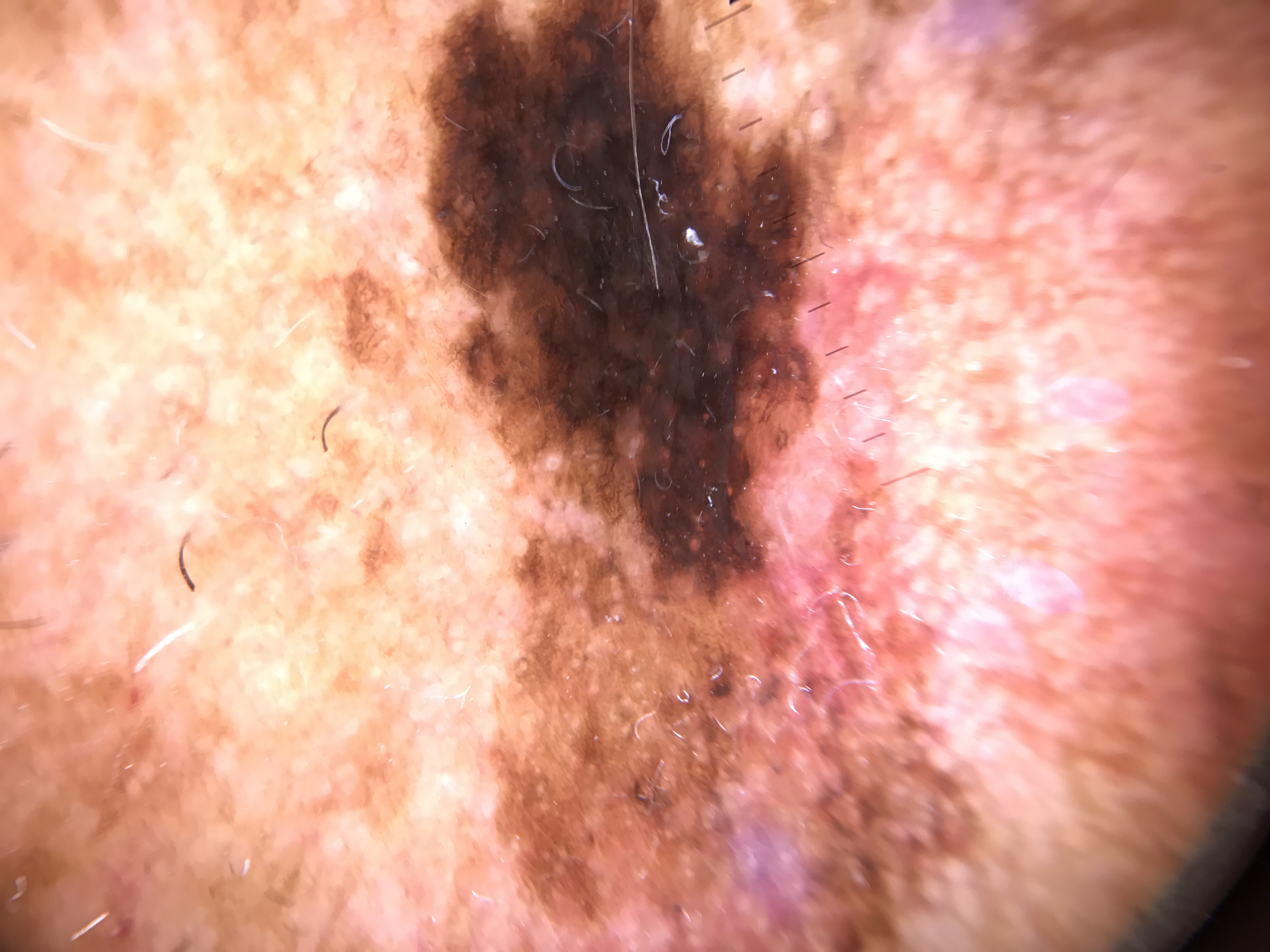pathology = lentigo maligna (biopsy-proven)